A dermatoscopic image of a skin lesion:
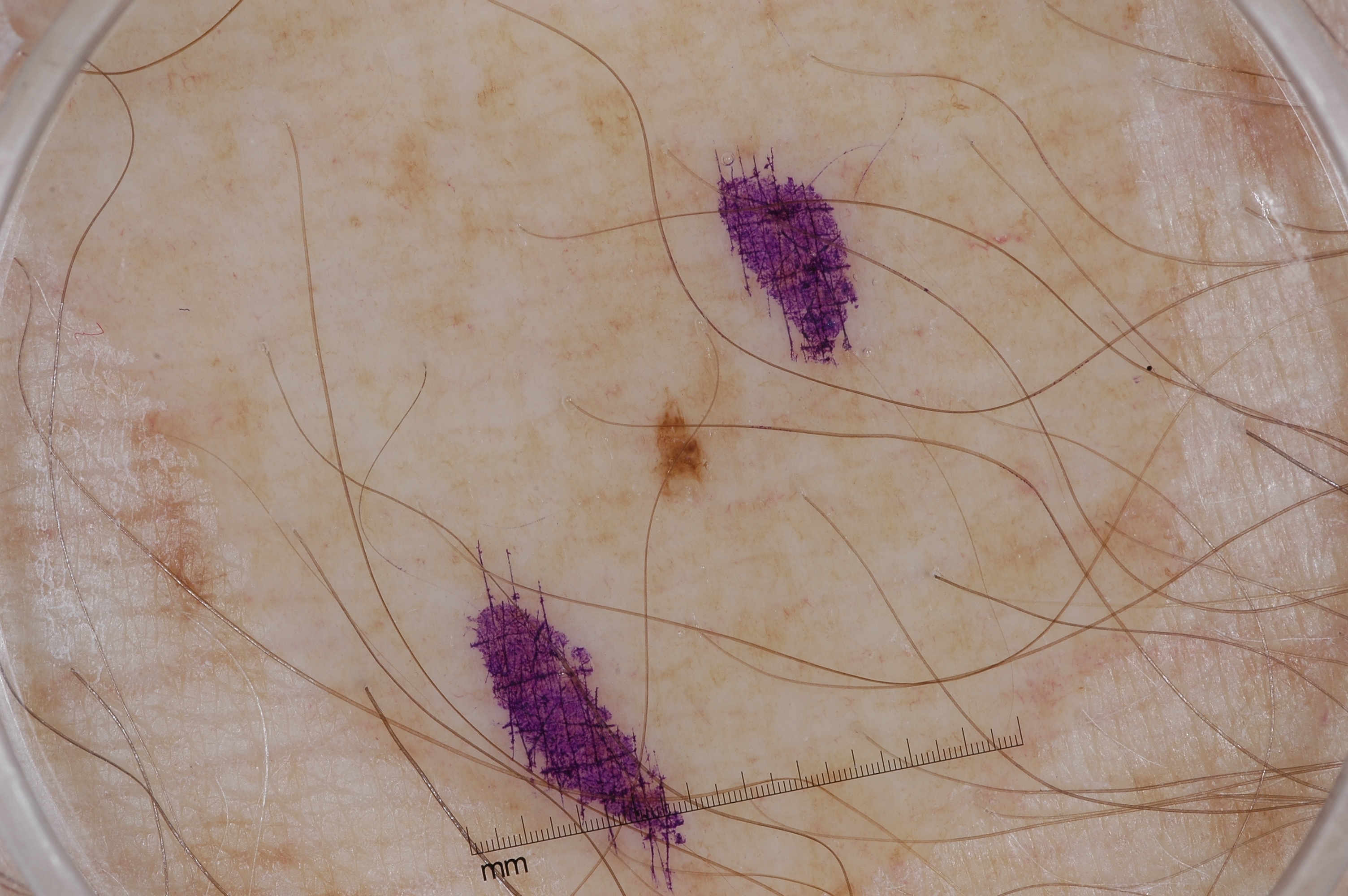dermoscopic features not present: milia-like cysts, pigment network, negative network, and streaks
lesion size: small
bounding box: <box>642, 387, 718, 515</box>
assessment: a melanocytic nevus, a benign skin lesion